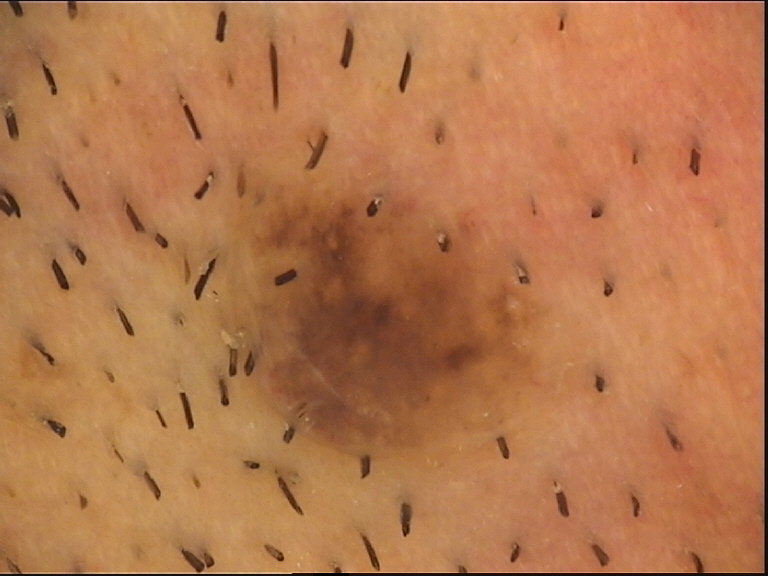imaging: dermoscopy; classification: banal; diagnosis: compound nevus (expert consensus).